A male subject, aged around 70. A dermoscopic image of a skin lesion: 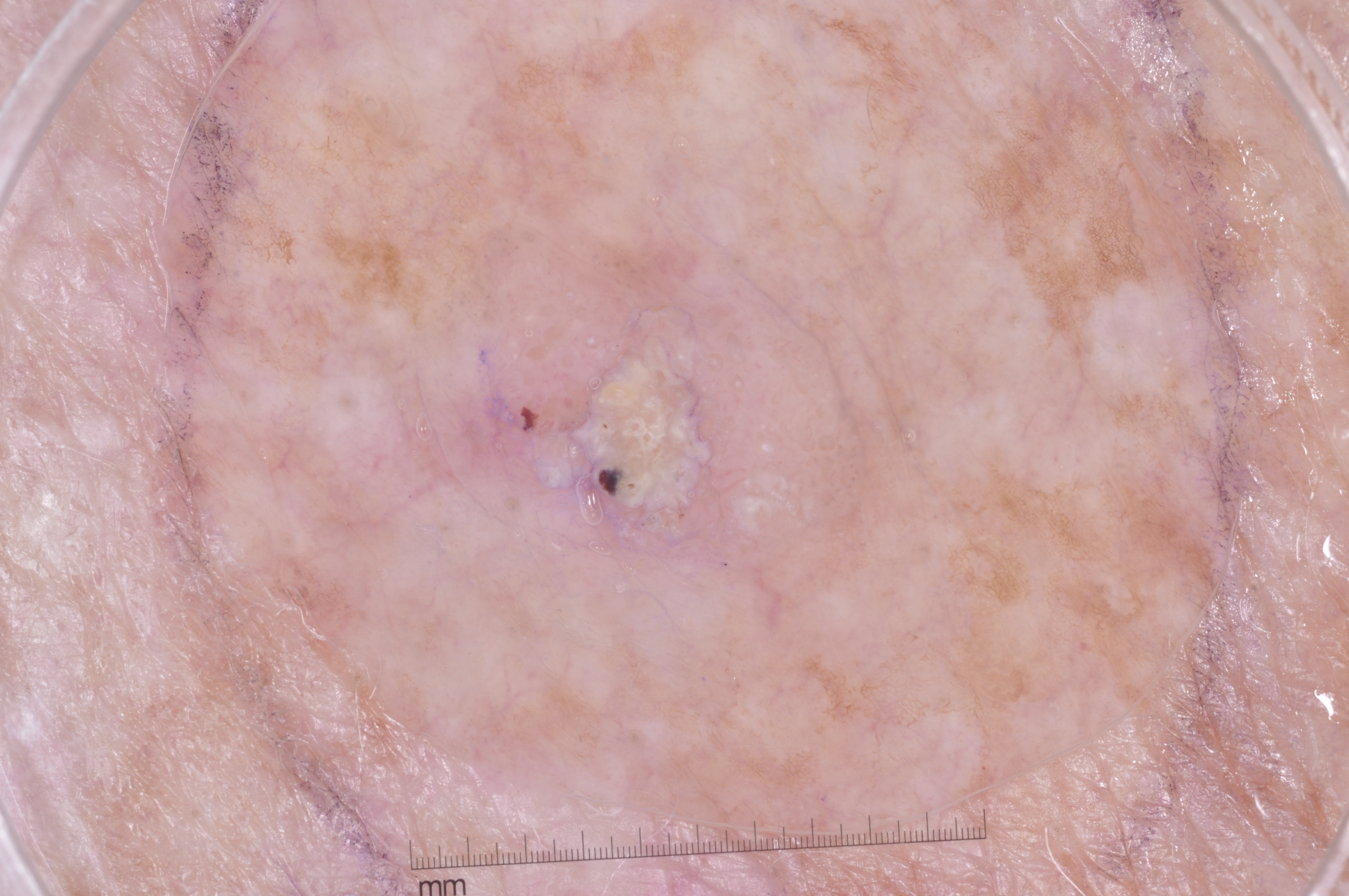Findings:
Dermoscopy demonstrates milia-like cysts. With coordinates (x1, y1, x2, y2), the lesion occupies the region bbox(398, 193, 871, 572). The lesion covers approximately 11% of the dermoscopic field.
Assessment:
Diagnosed as a seborrheic keratosis, a benign lesion.